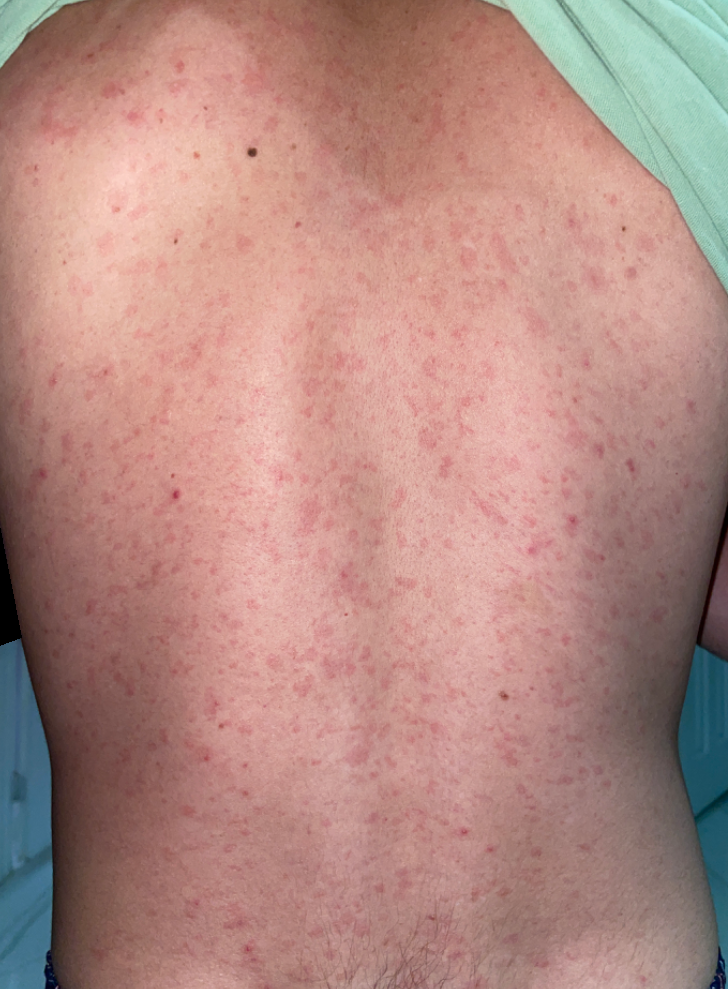  patient: male, age 18–29
  body_site:
    - head or neck
    - front of the torso
    - back of the torso
  shot_type: close-up
  differential:
    leading:
      - Drug Rash
    considered:
      - Viral Exanthem